A male patient, aged 68-72 · a skin lesion imaged with a dermatoscope:
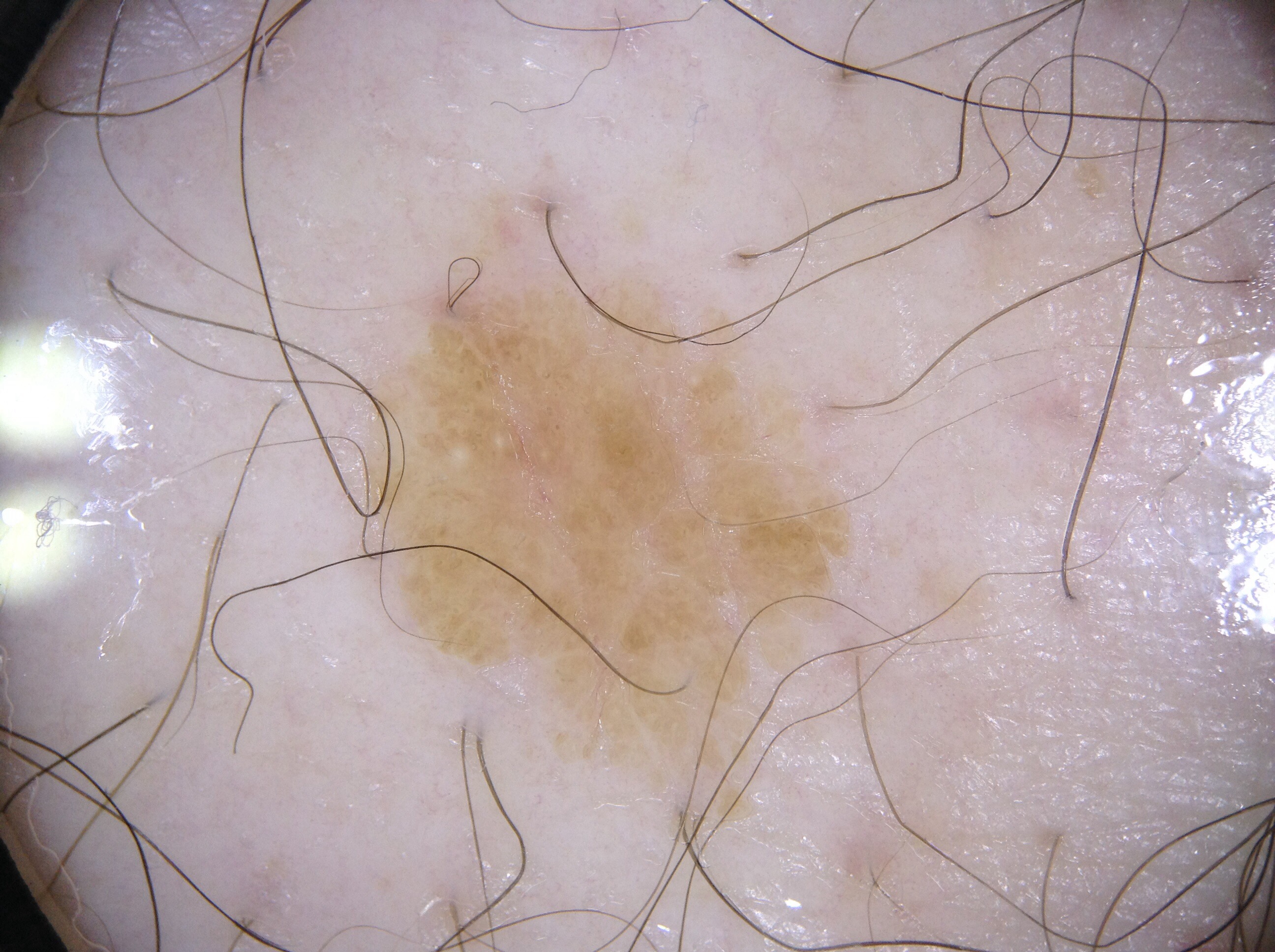<dermoscopy>
<dermoscopic_features>
  <present>milia-like cysts</present>
  <absent>streaks, negative network, pigment network</absent>
</dermoscopic_features>
<lesion_extent>
  <approx_field_fraction_pct>11</approx_field_fraction_pct>
</lesion_extent>
<lesion_location>
  <bbox_xyxy>369, 283, 837, 706</bbox_xyxy>
</lesion_location>
<diagnosis>
  <name>seborrheic keratosis</name>
  <malignancy>benign</malignancy>
  <lineage>keratinocytic</lineage>
  <provenance>clinical</provenance>
</diagnosis>
</dermoscopy>